Located on the top or side of the foot and leg; the photo was captured at an angle; the contributor is 60–69, female.
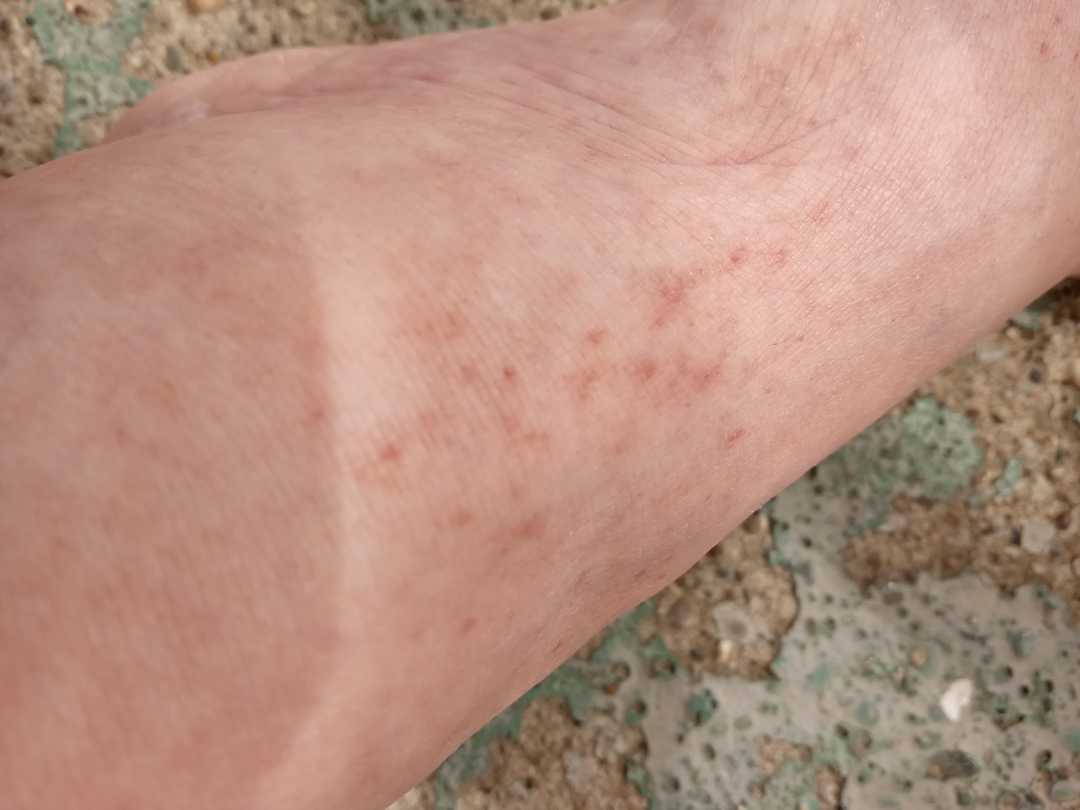Scabies and Acute dermatitis, NOS were considered with similar weight.